The photograph is a close-up of the affected area:
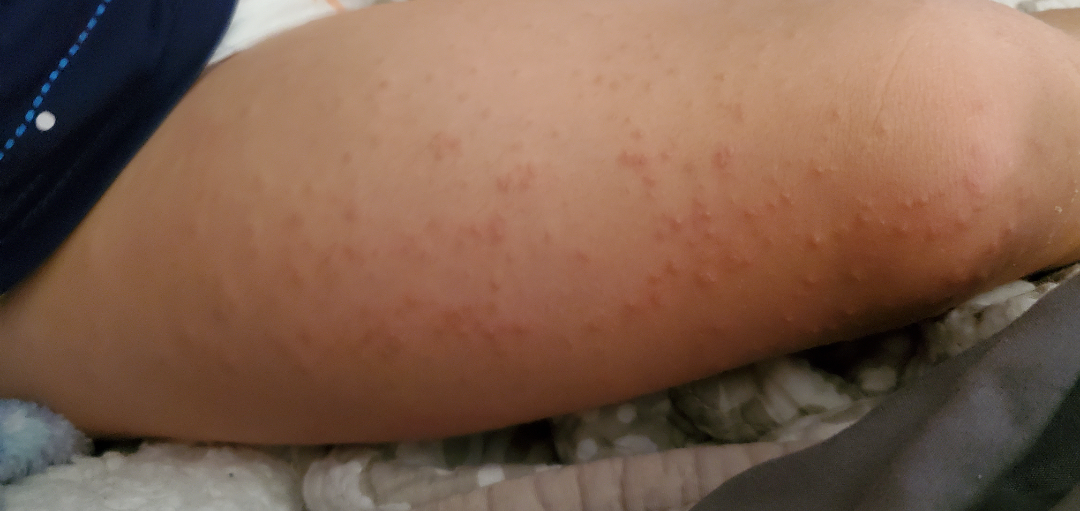Miliaria (33%); Folliculitis (33%); Molluscum Contagiosum (33%).